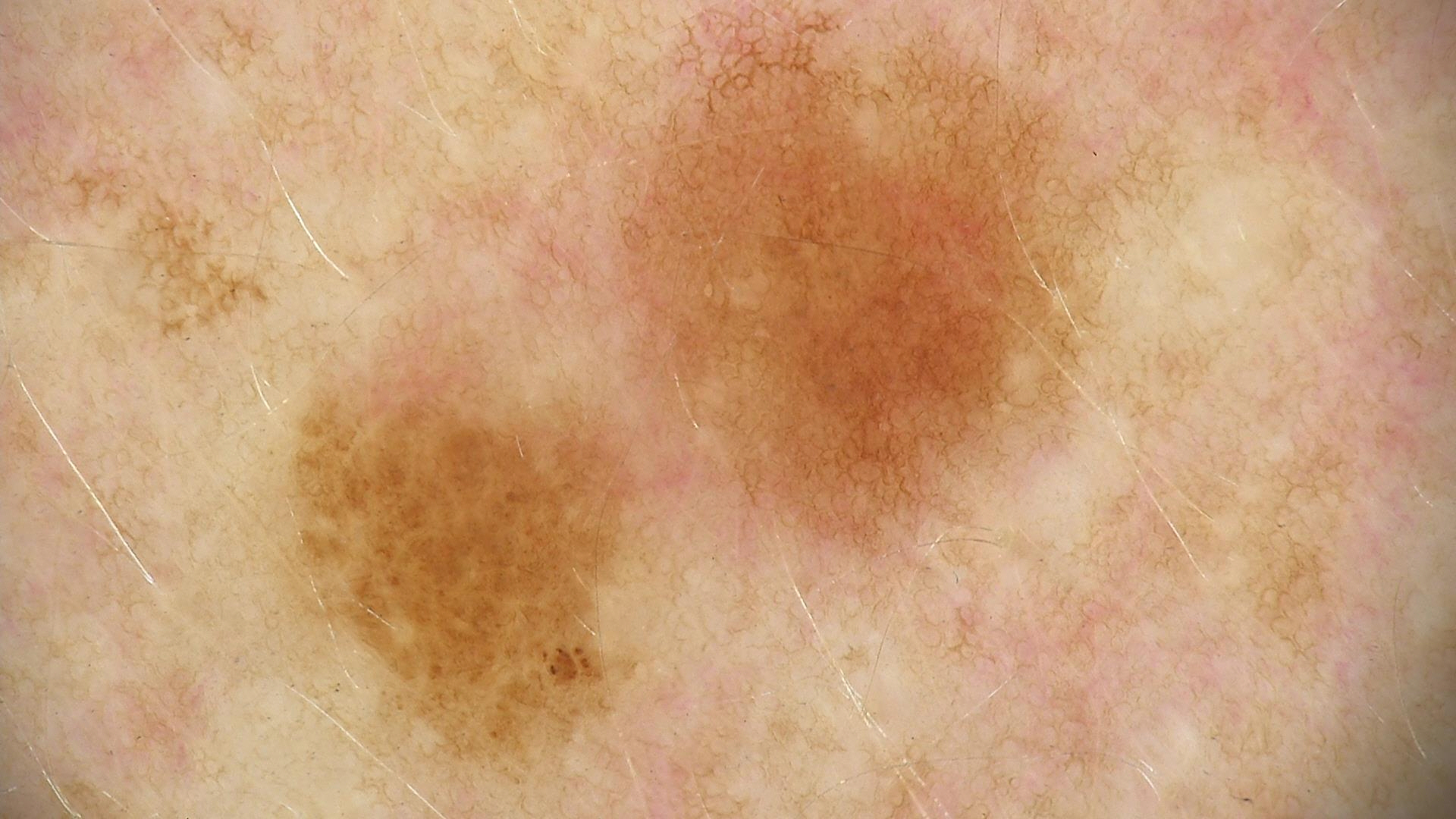A skin lesion imaged with a dermatoscope. Consistent with a benign lesion — a dysplastic junctional nevus.